This is a close-up image; reported duration is less than one week; located on the front of the torso; the lesion is described as raised or bumpy; symptoms reported: itching: 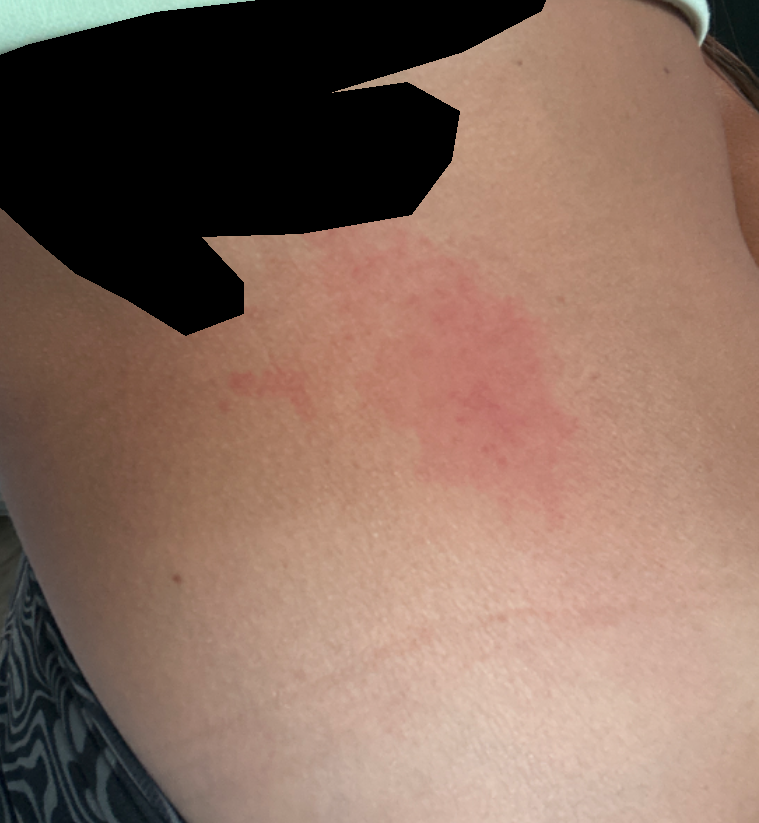The skin condition could not be confidently assessed from this image.